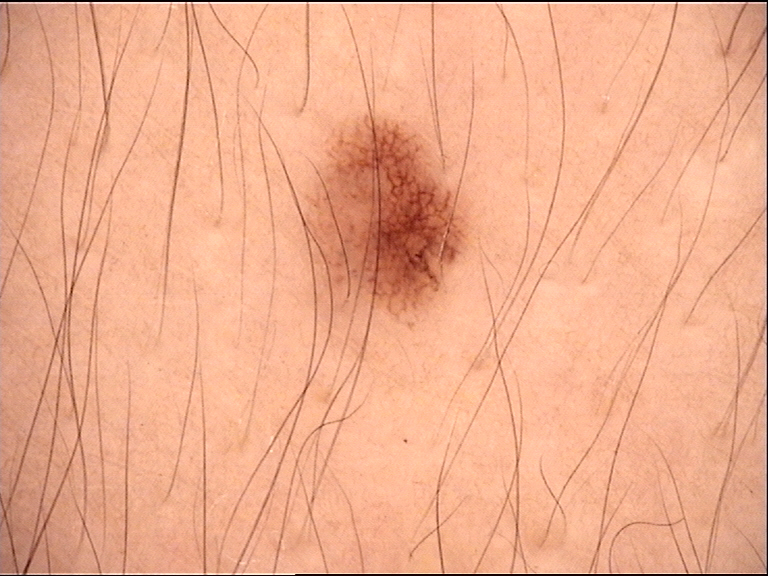{
  "image": "dermatoscopy",
  "diagnosis": {
    "name": "dysplastic junctional nevus",
    "code": "jd",
    "malignancy": "benign",
    "super_class": "melanocytic",
    "confirmation": "expert consensus"
  }
}